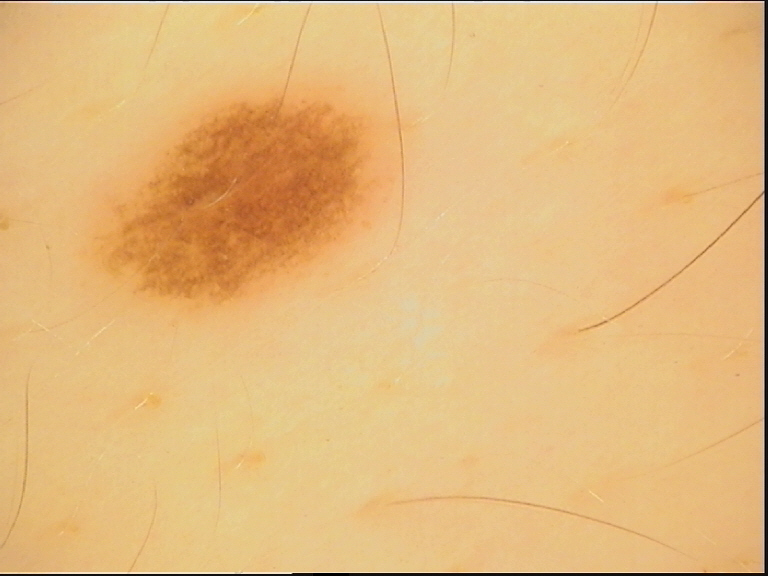A dermoscopic photograph of a skin lesion.
Labeled as a dysplastic junctional nevus.